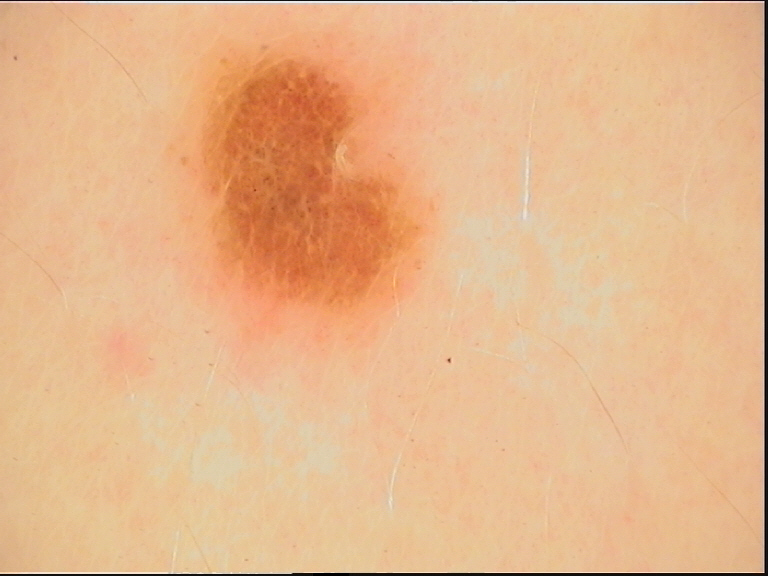diagnosis: dysplastic compound nevus (expert consensus)